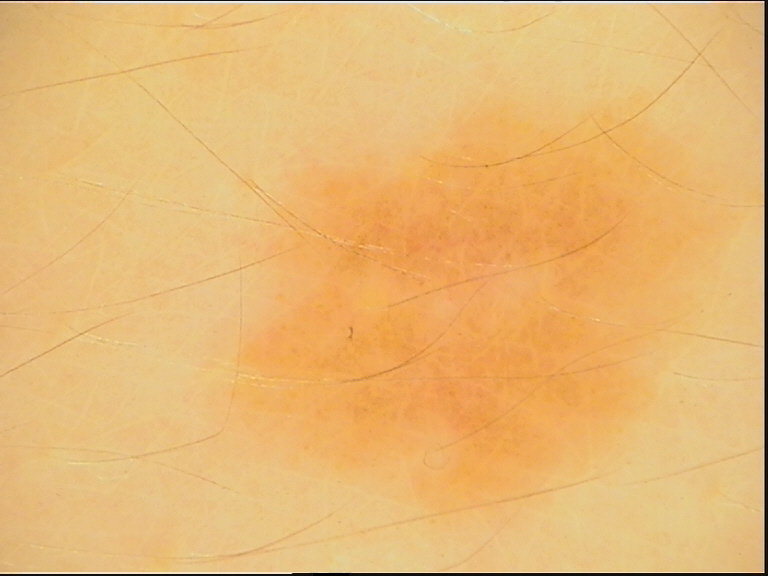diagnosis: dysplastic junctional nevus (expert consensus).